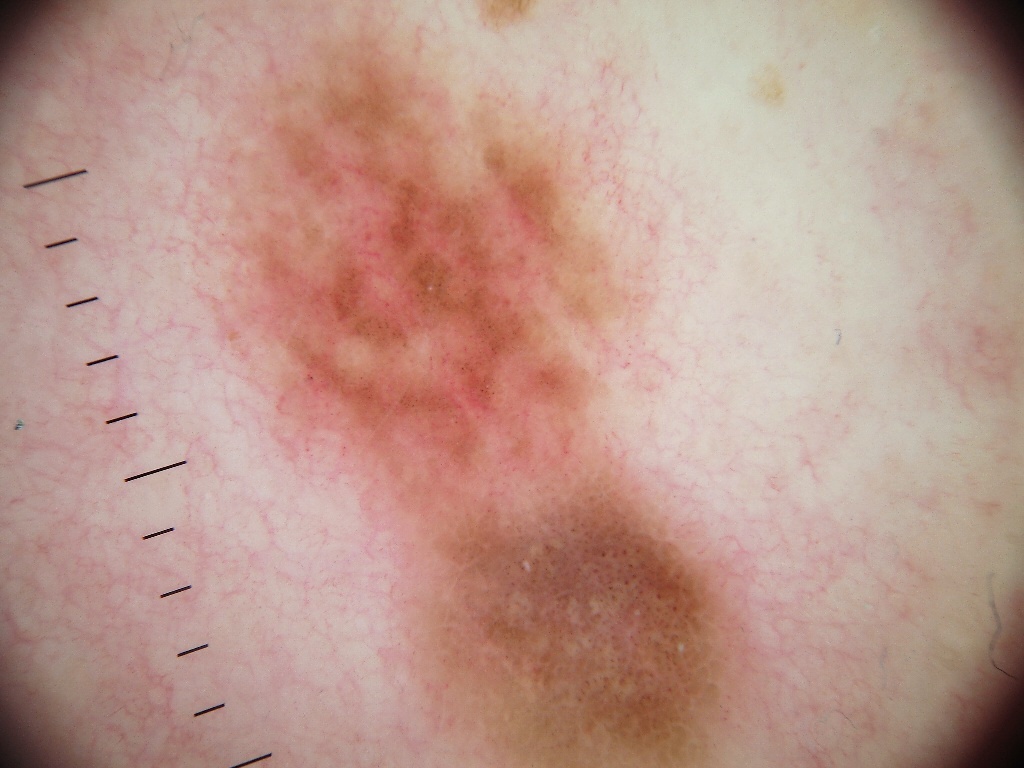Case summary: A female subject about 30 years old. This is a dermoscopic photograph of a skin lesion. In (x1, y1, x2, y2) order, the lesion occupies the region [161, 14, 785, 766]. A prominent lesion filling much of the field. On dermoscopy, the lesion shows negative network, milia-like cysts, and globules. Conclusion: Consistent with a melanocytic nevus, a benign lesion.